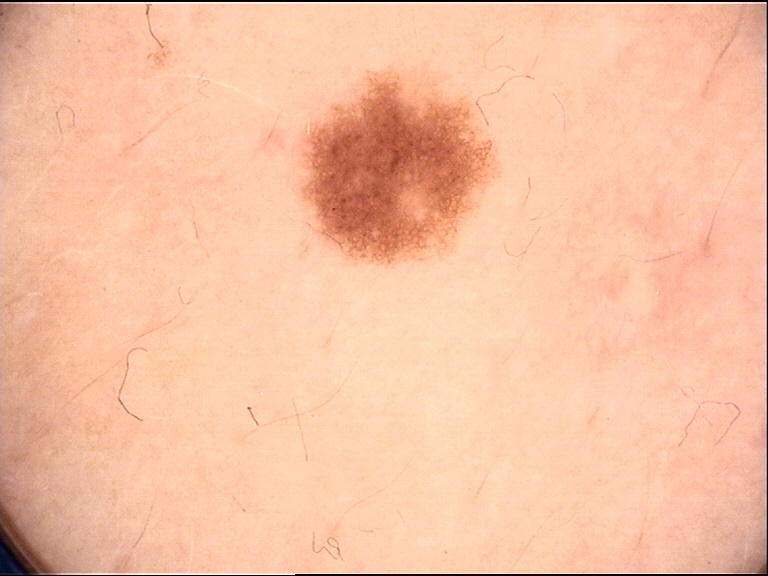Q: What kind of image is this?
A: dermoscopy
Q: What was the diagnostic impression?
A: dysplastic junctional nevus (expert consensus)